The chart records prior skin cancer (patient or family) and prior malignancy (patient or family) · a smartphone photograph of a skin lesion · the patient was assessed as skin type II · a female subject 59 years old: 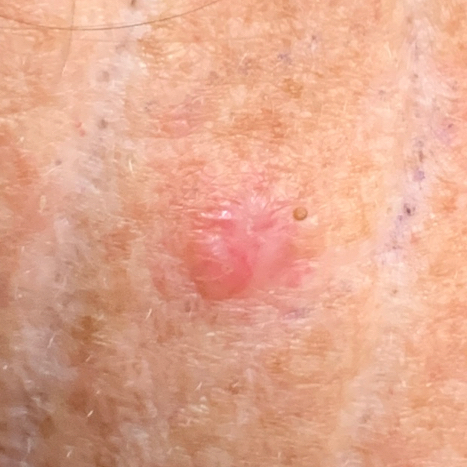Q: What is the anatomic site?
A: the neck
Q: How large is the lesion?
A: approx. 7 × 6 mm
Q: Any reported symptoms?
A: elevation
Q: What is the diagnosis?
A: basal cell carcinoma (biopsy-proven)